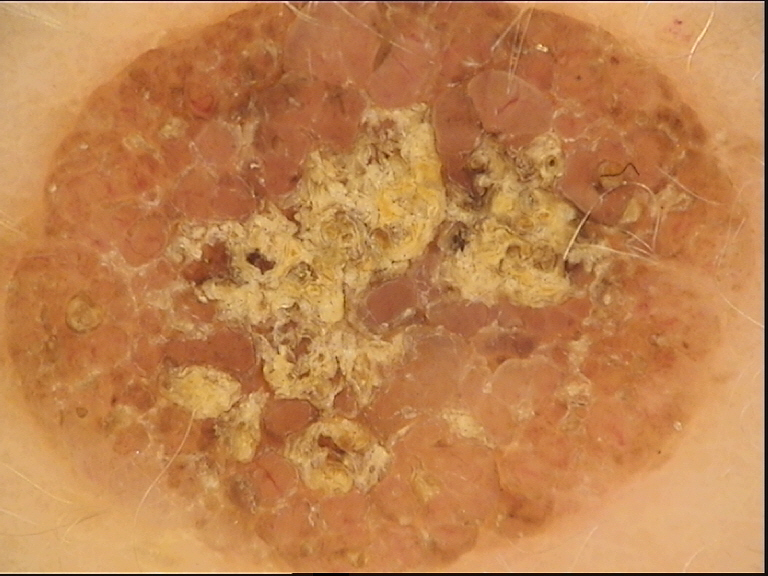Findings:
A dermoscopic photograph of a skin lesion. This is a banal lesion.
Conclusion:
The diagnostic label was a dermal nevus.